A dermoscopic close-up of a skin lesion:
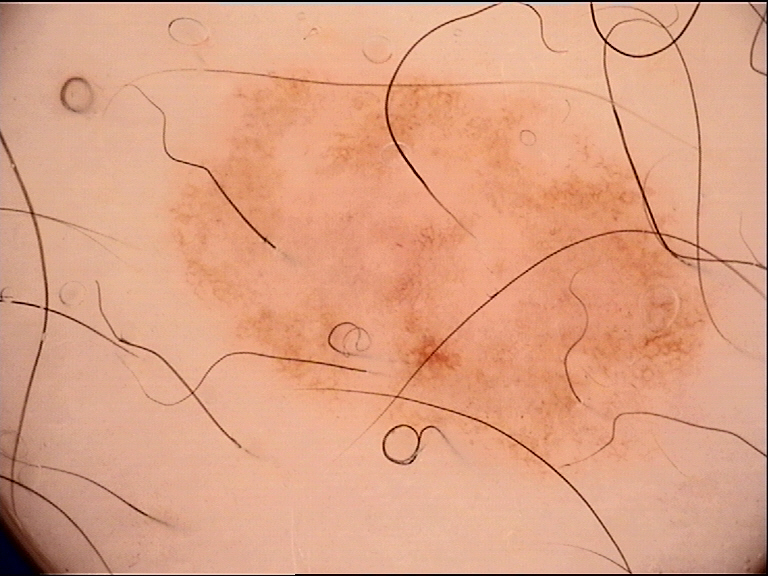<lesion>
<diagnosis>
<name>dysplastic junctional nevus</name>
<code>jd</code>
<malignancy>benign</malignancy>
<super_class>melanocytic</super_class>
<confirmation>expert consensus</confirmation>
</diagnosis>
</lesion>